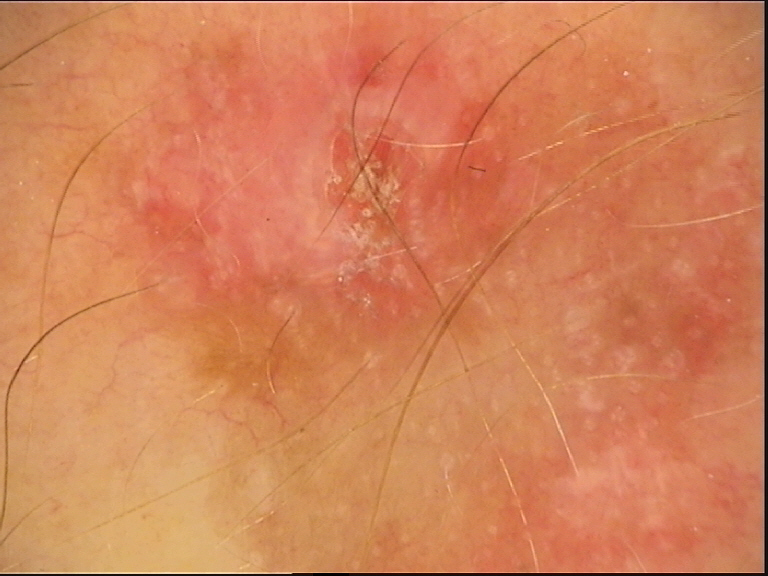Consistent with a keratinocytic lesion — an actinic keratosis.